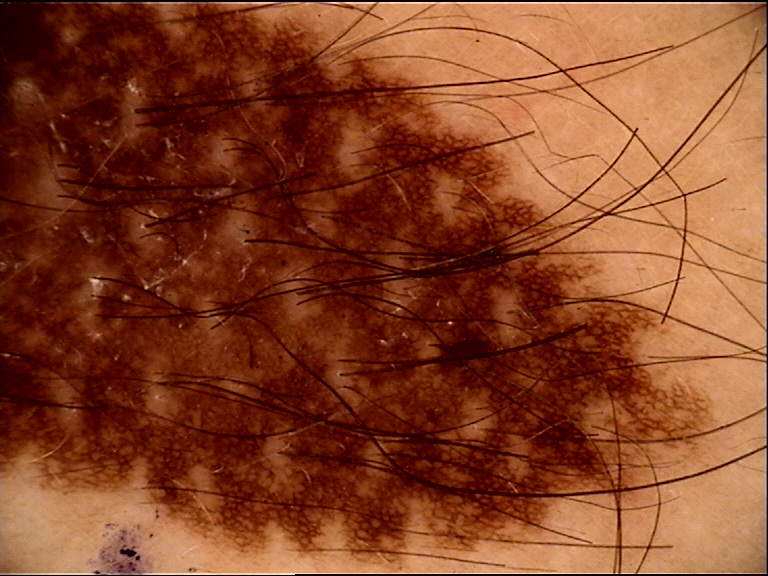label: congenital compound nevus (expert consensus).